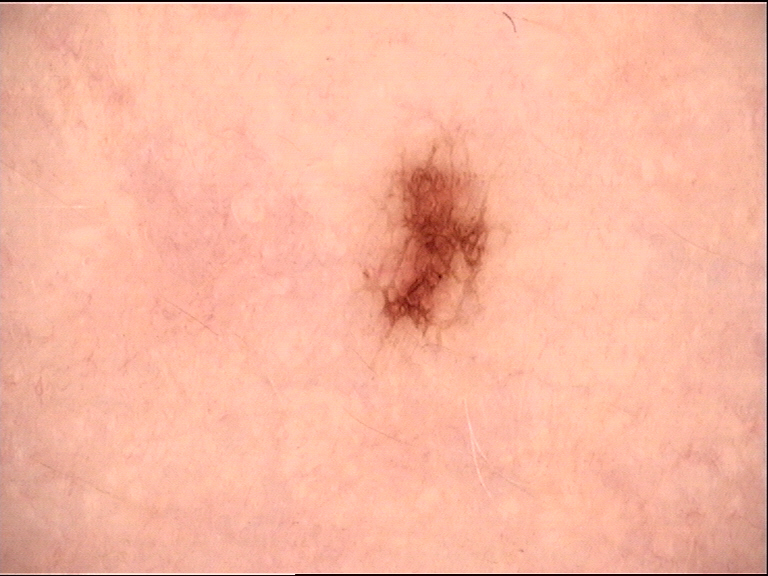Q: What was the diagnostic impression?
A: dysplastic junctional nevus (expert consensus)